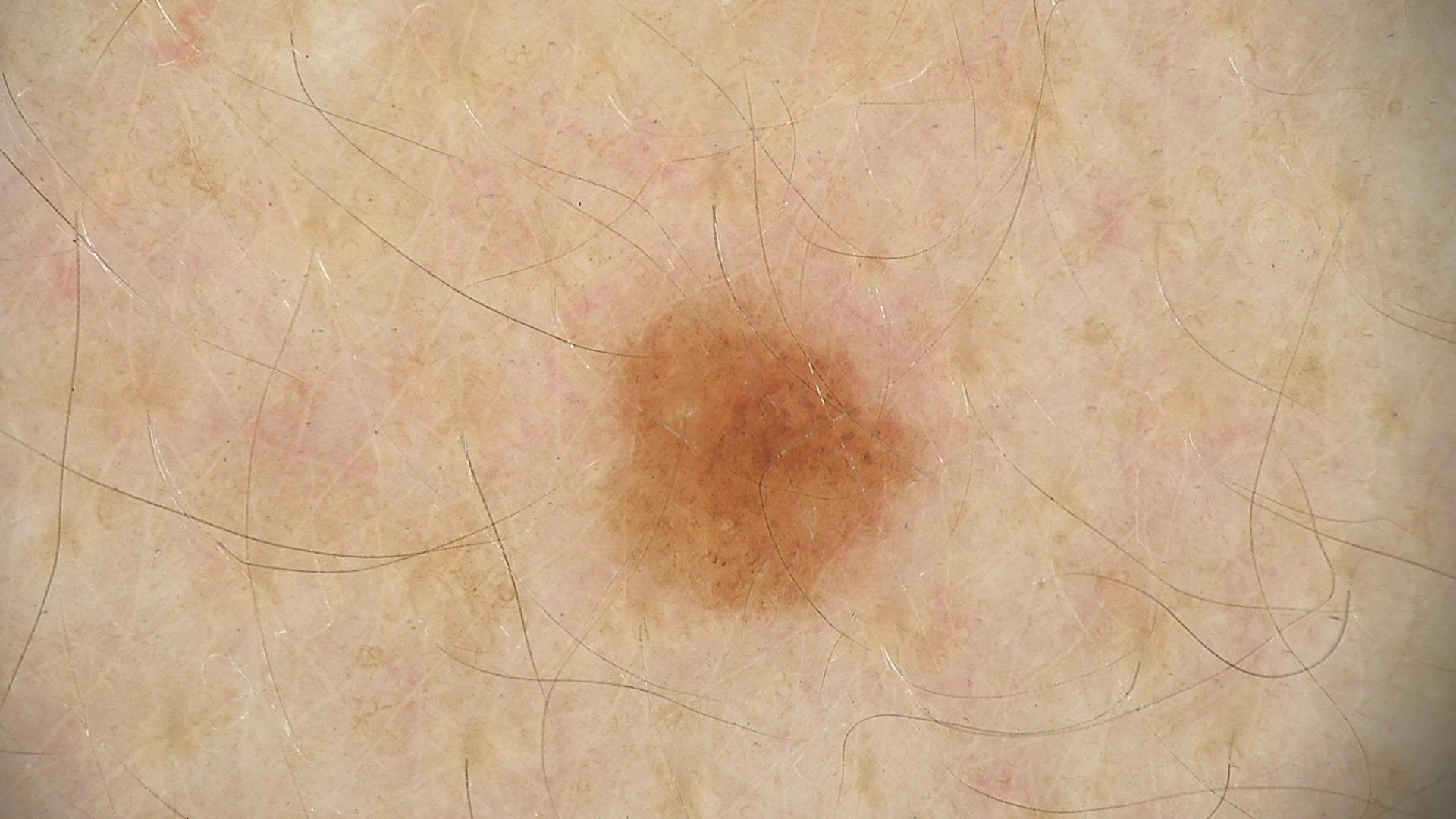Classified as a dysplastic junctional nevus.